A male subject in their early 70s; the chart records prior malignancy (patient or family) and no prior skin cancer (patient or family); a clinical photo of a skin lesion taken with a smartphone — 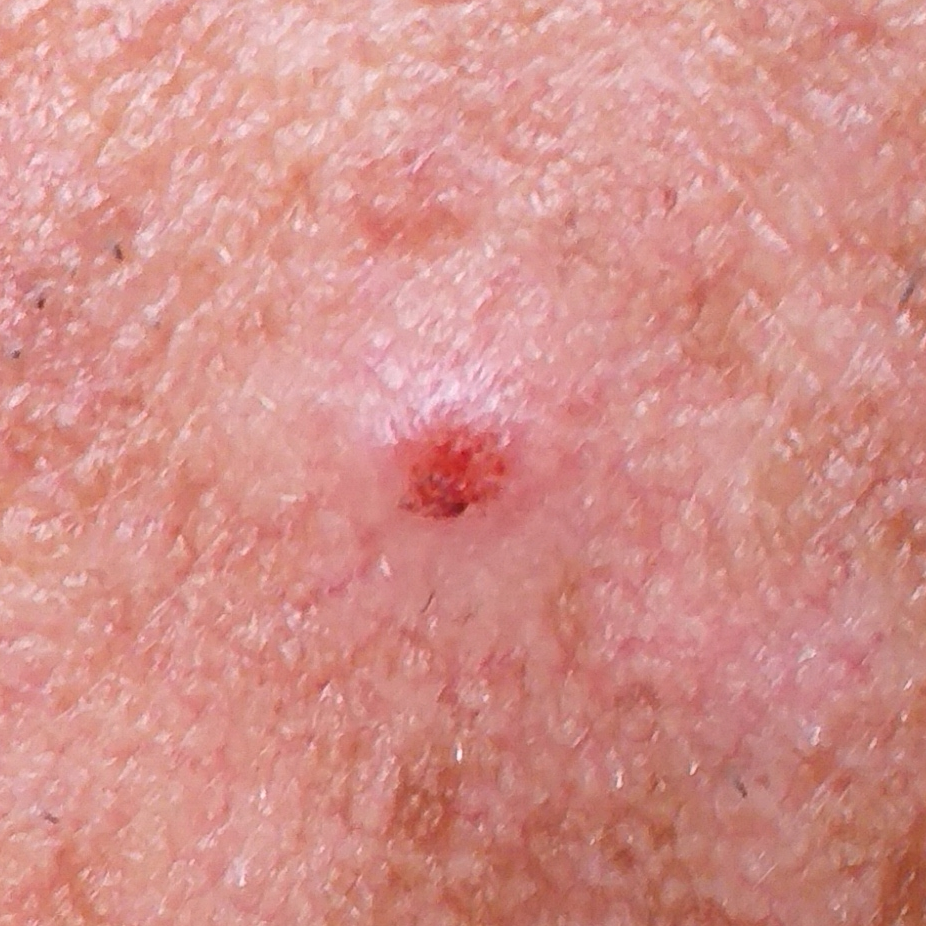Case summary: Measuring about 5 × 5 mm. The patient reports that the lesion has bled, itches, is elevated, and hurts. Pathology: The biopsy diagnosis was an actinic keratosis.